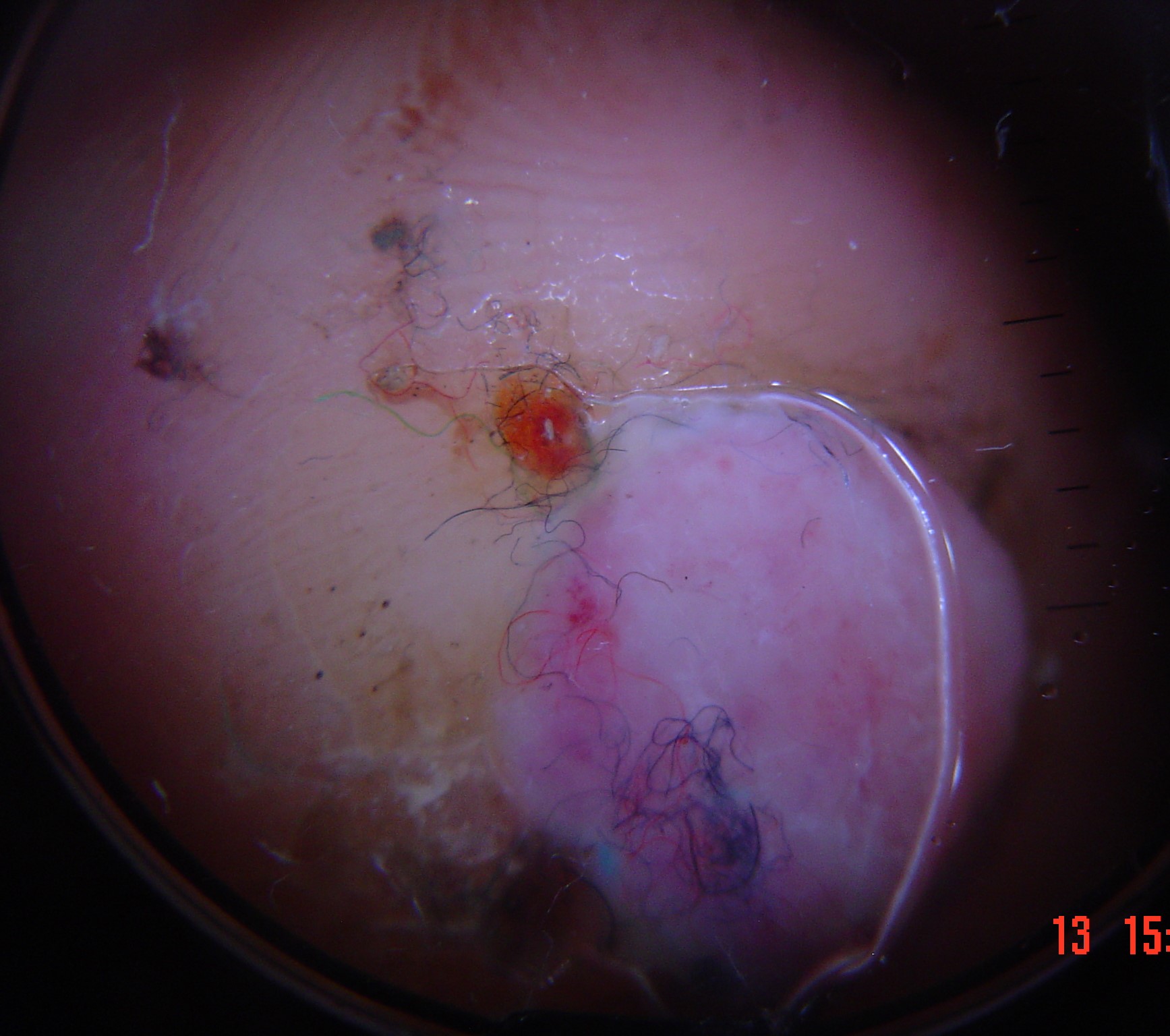Conclusion:
The biopsy diagnosis was a malignancy — an acral nodular melanoma.